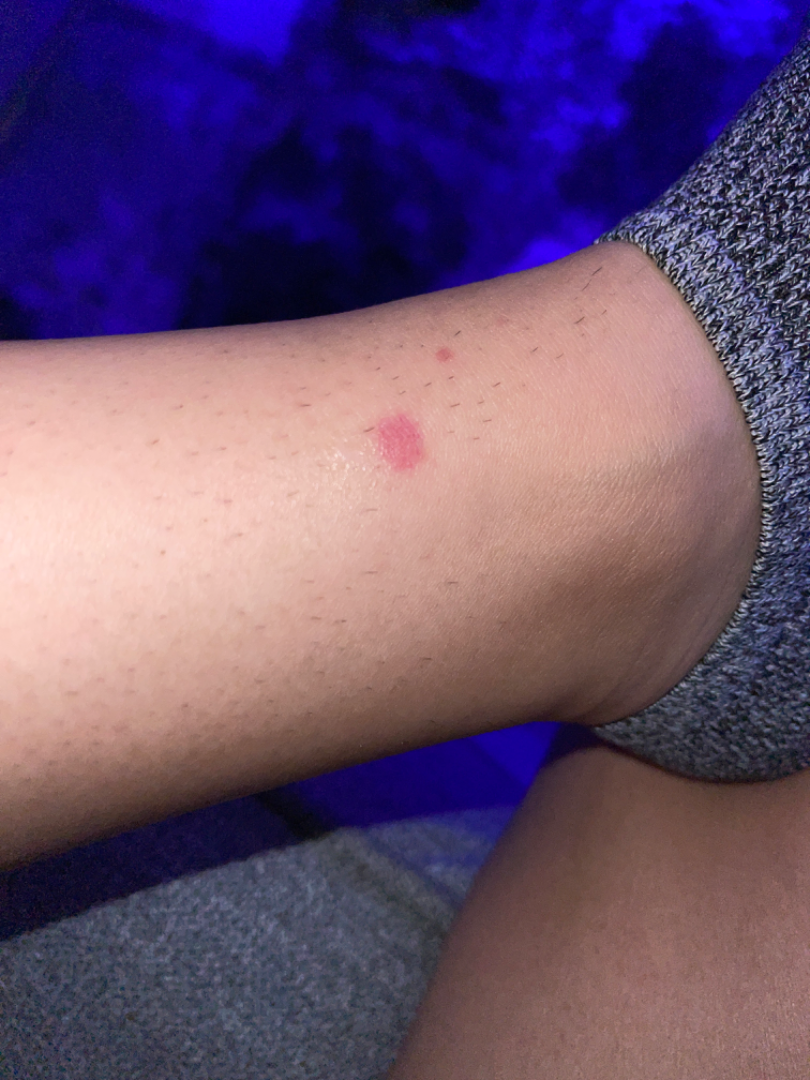The patient is 18–29, female. The lesion involves the leg. The photo was captured at an angle. Most consistent with Insect Bite; an alternative is Pigmented purpuric eruption; less likely is Leukemia cutis.